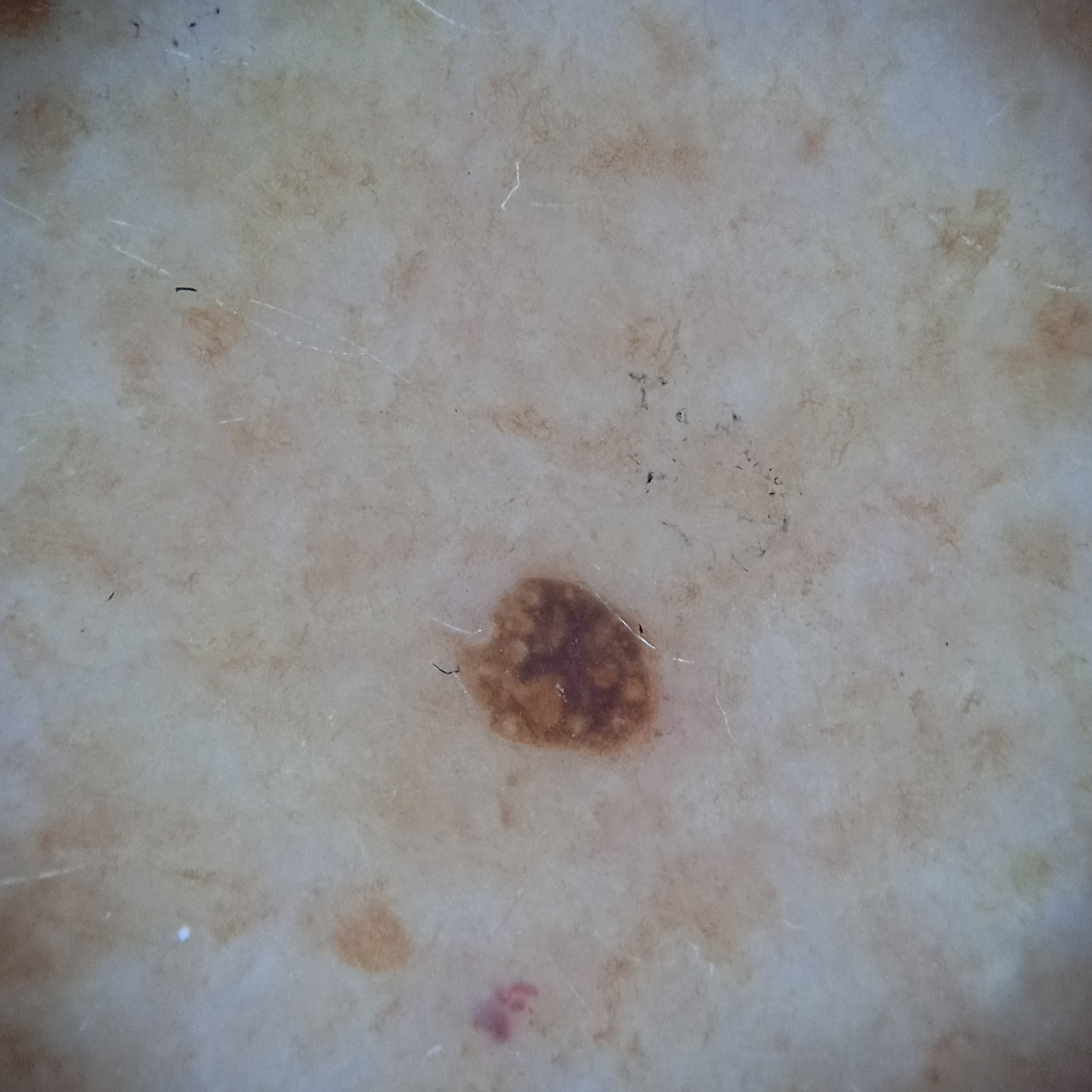Q: What is the imaging modality?
A: dermoscopic image
Q: Patient demographics?
A: female, age 78
Q: Why was this imaged?
A: research study (no referral diagnosis)
Q: Where is the lesion?
A: an arm
Q: Lesion size?
A: 2.4 mm
Q: What was the diagnosis?
A: seborrheic keratosis (dermatologist consensus)